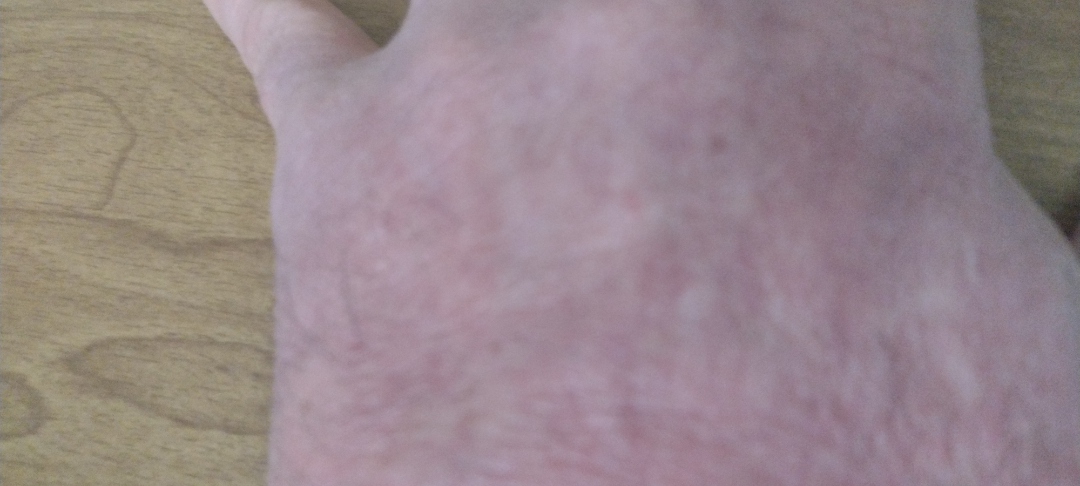Q: What is the differential diagnosis?
A: Eczema (considered); Allergic Contact Dermatitis (considered)